The photo was captured at a distance; the subject is a female aged 40–49; the lesion involves the top or side of the foot and leg — 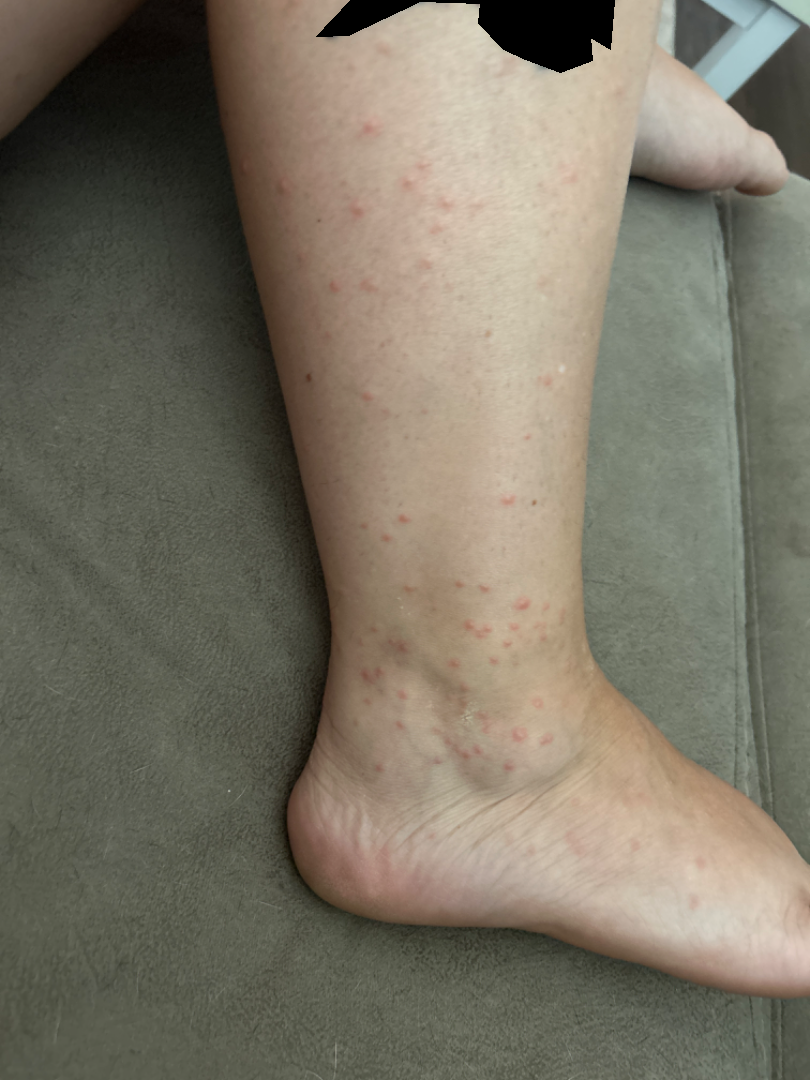| feature | finding |
|---|---|
| onset | one to four weeks |
| other reported symptoms | none reported |
| patient describes the issue as | skin that appeared healthy to them |
| described texture | raised or bumpy |
| impression | in keeping with Insect Bite |